A dermoscopy image of a single skin lesion: 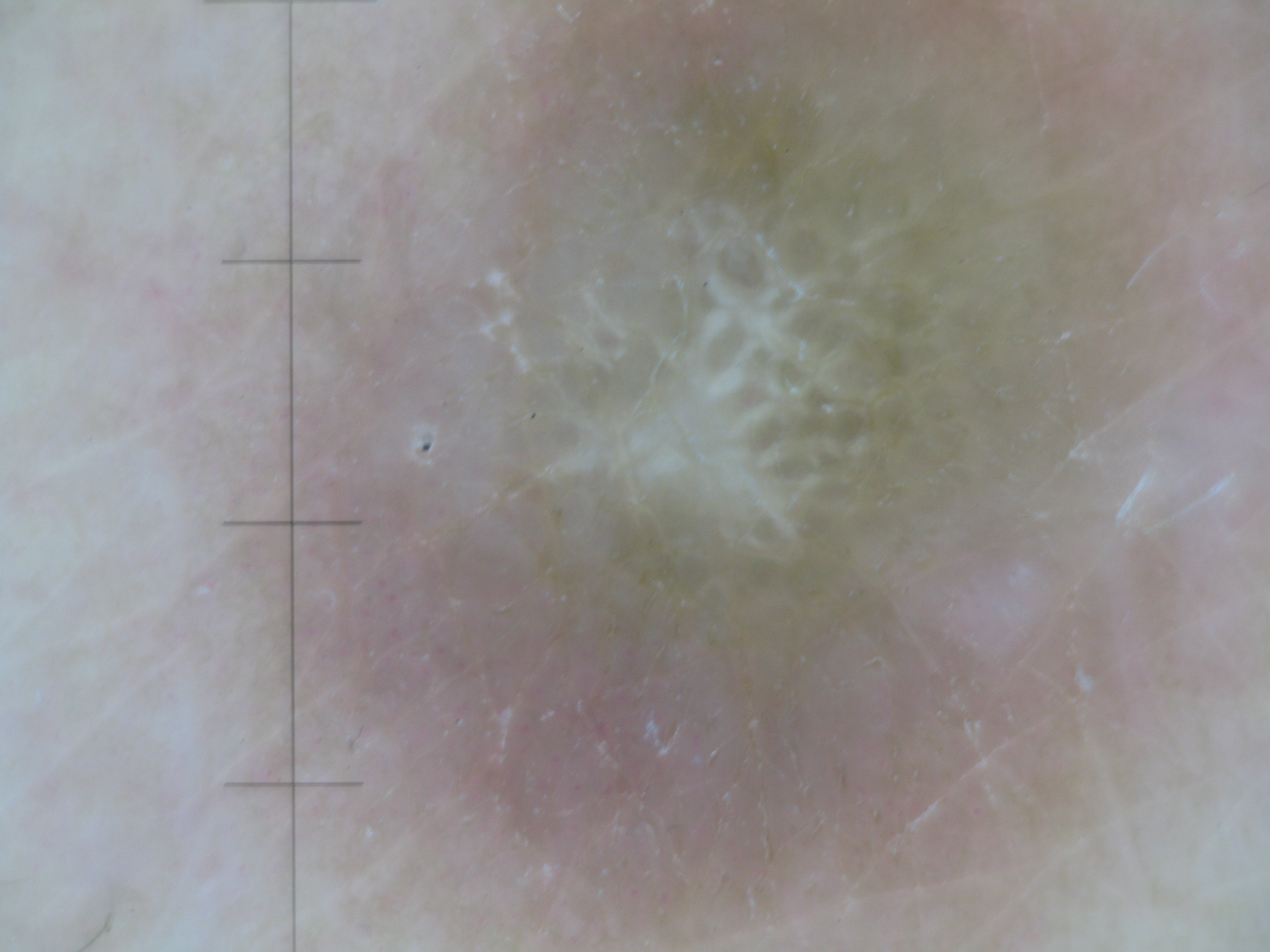Findings:
The architecture is that of a fibro-histiocytic lesion.
Impression:
The diagnosis was a dermatofibroma.